A subject in their 40s. A smartphone photograph of a skin lesion — 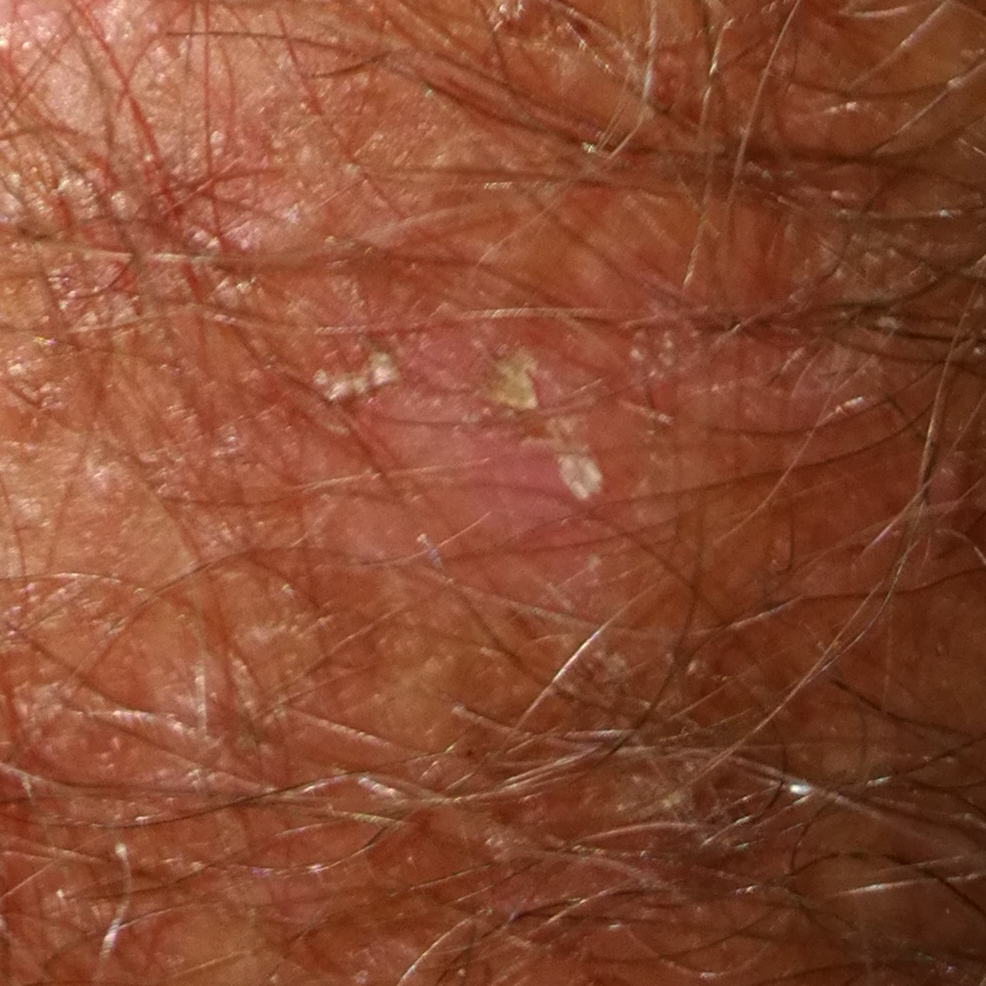Notes:
– anatomic site — a forearm
– patient-reported symptoms — itching
– assessment — actinic keratosis (clinical consensus)